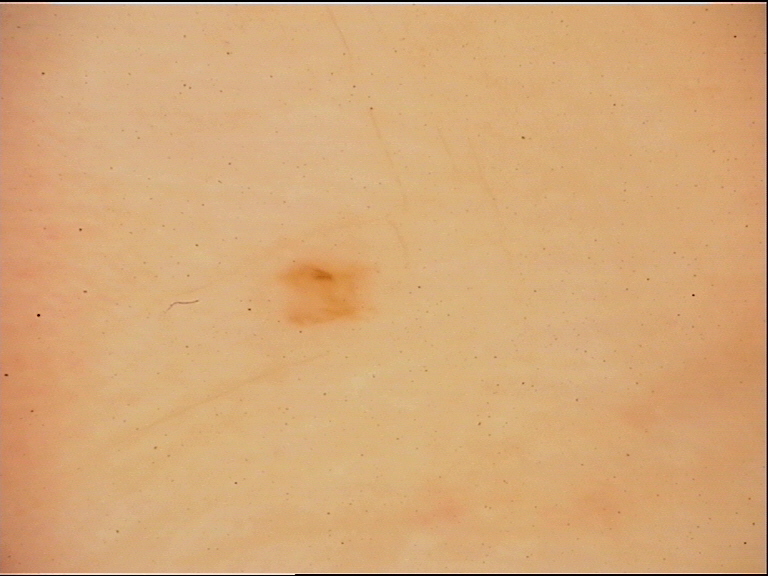classification — banal | class — acral junctional nevus (expert consensus).